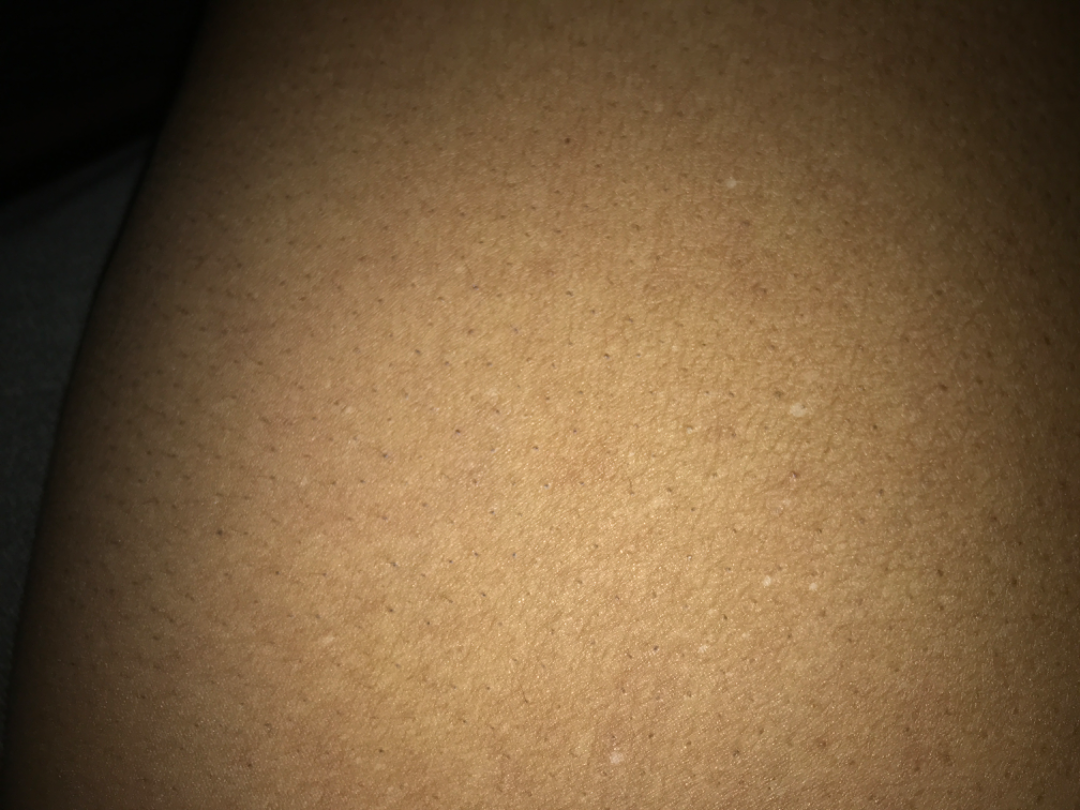Findings: The skin findings could not be characterized from the image. Background: Skin tone: Fitzpatrick skin type V. The photograph was taken at a distance.